A female patient aged 33 to 37. Per the chart, a prior melanoma. Recorded as skin type II — 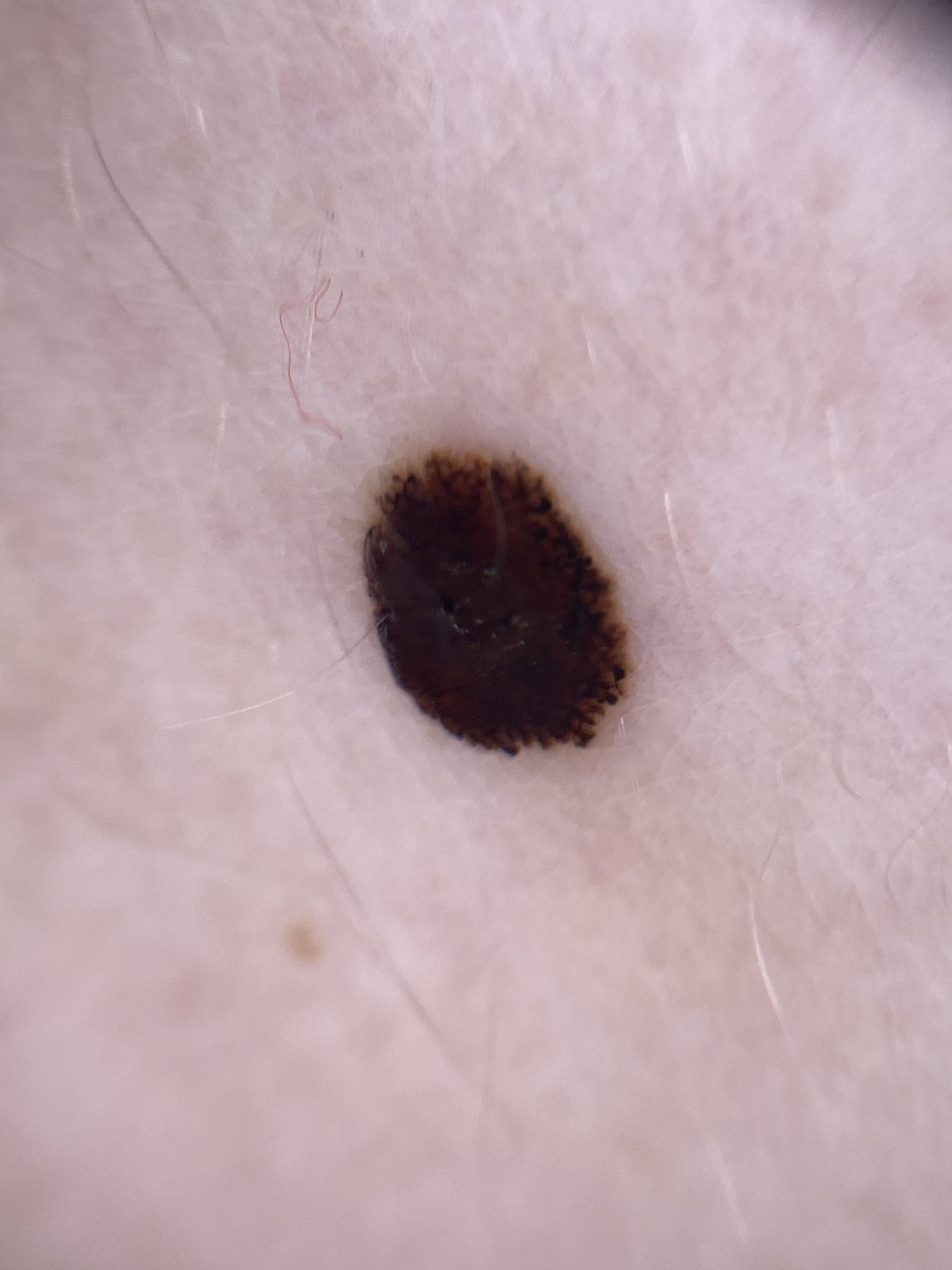Image and clinical context: The lesion was found on the trunk (the anterior trunk). Pathology: The biopsy diagnosis was a melanoma.